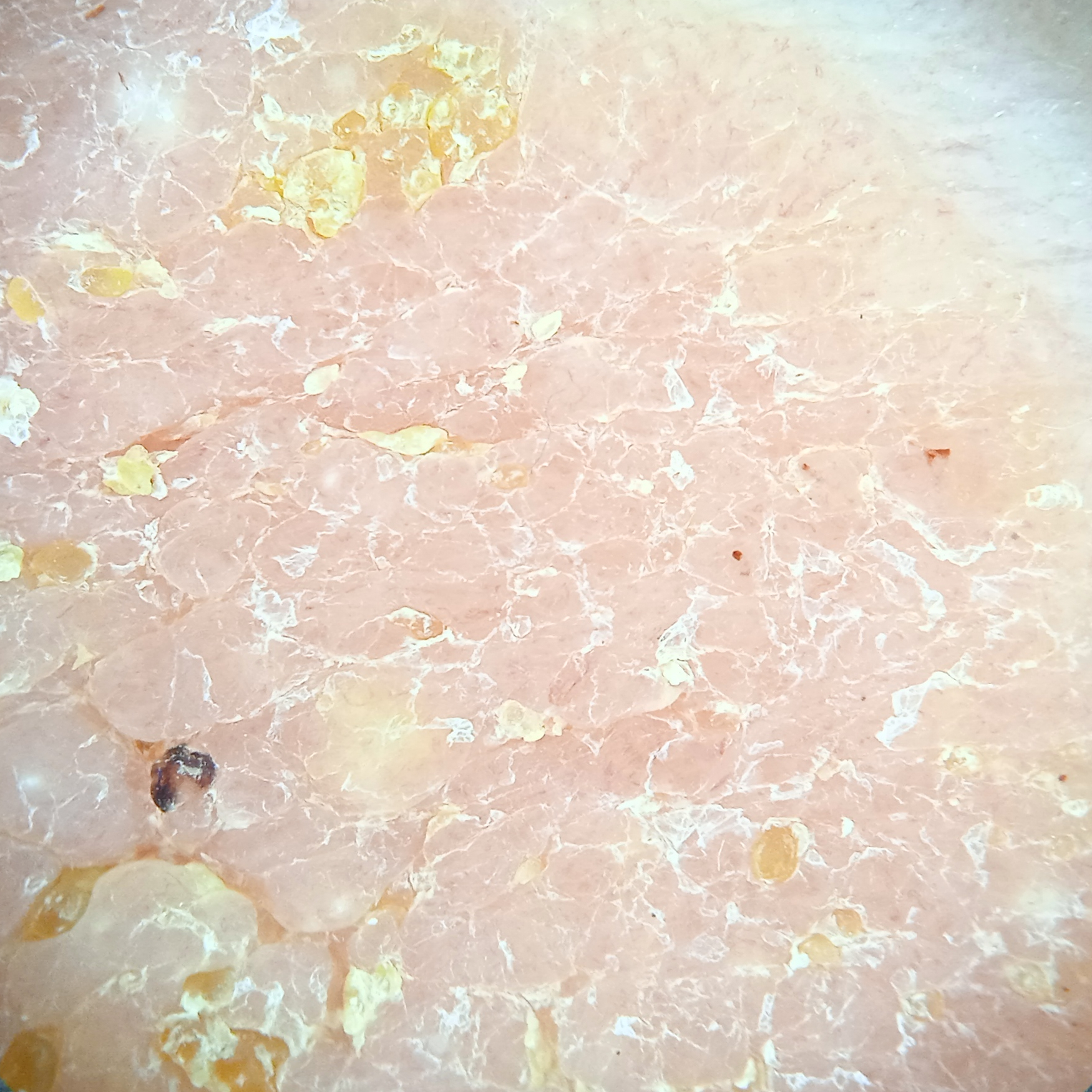Findings:
– patient · female, 81 years of age
– referral · research study (no referral diagnosis)
– site · the torso
– lesion size · 31 mm
– assessment · seborrheic keratosis (dermatologist consensus)